A dermoscopic close-up of a skin lesion: 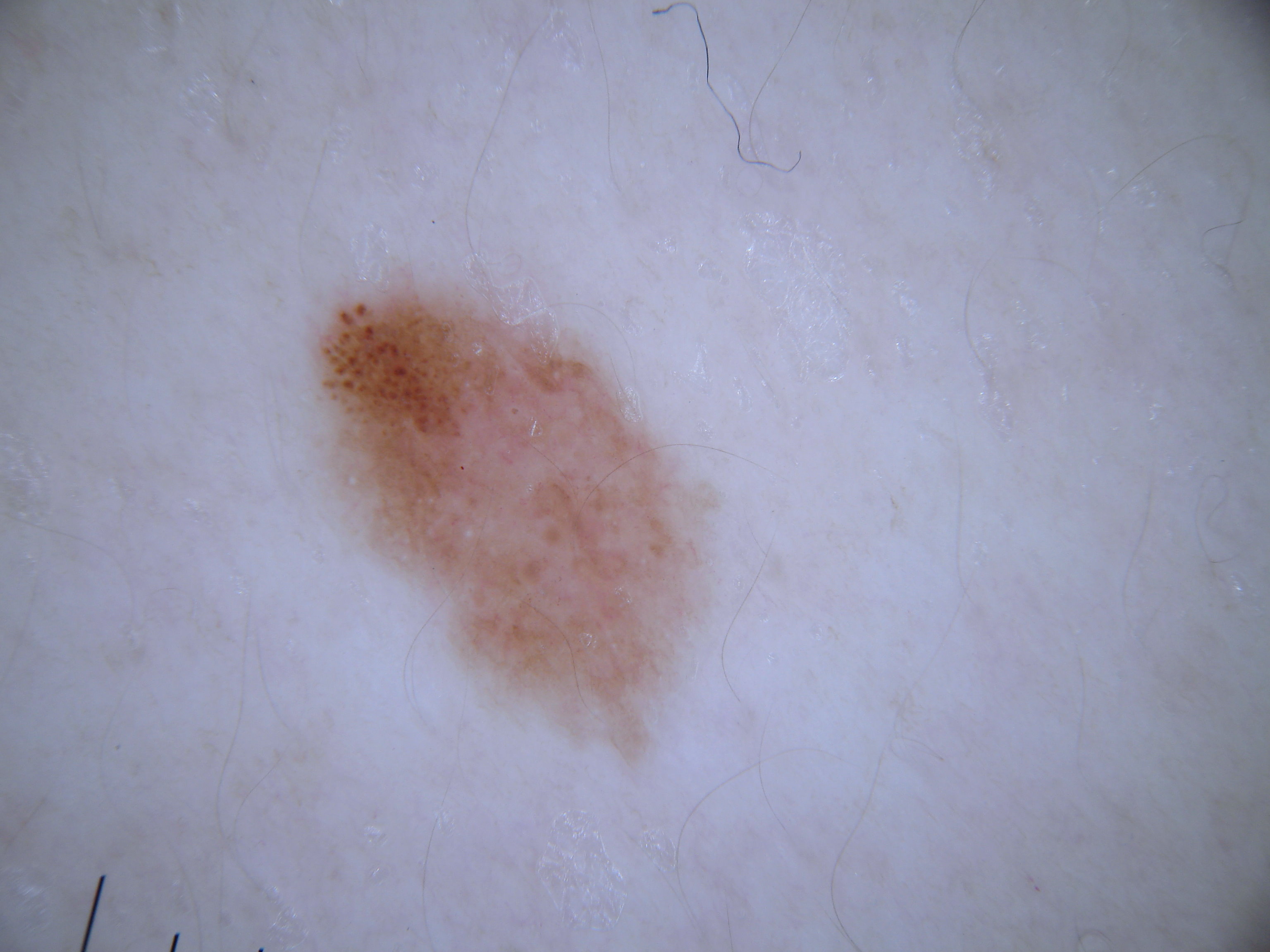Case summary:
The lesion takes up a moderate portion of the field. In (x1, y1, x2, y2) order, lesion location: [305,266,711,764]. Dermoscopic assessment notes globules.
Impression:
Consistent with a melanocytic nevus.